This is a close-up image.
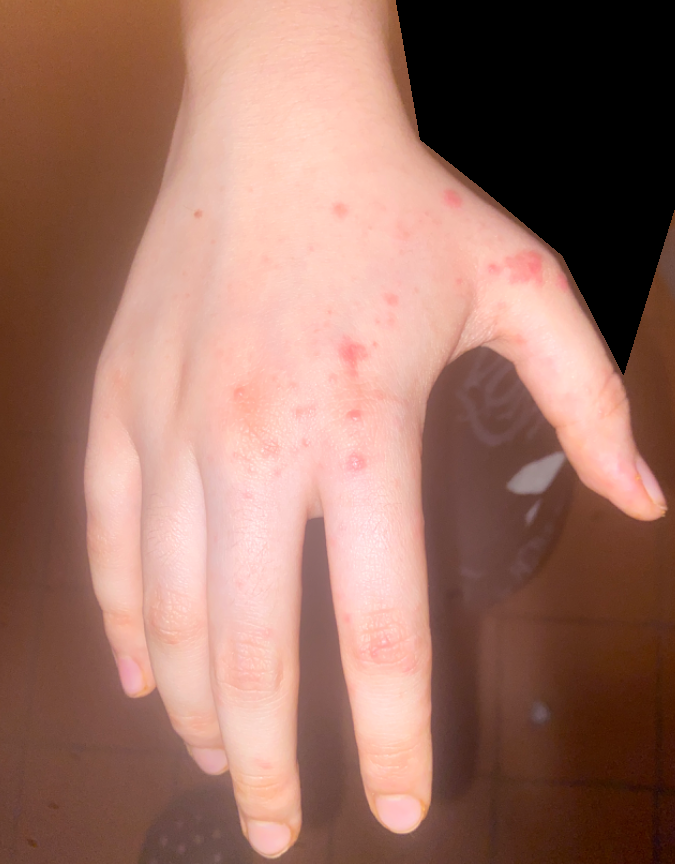Impression:
On remote dermatologist review, Impetigo (weight 0.33); Molluscum Contagiosum (weight 0.33); Allergic Contact Dermatitis (weight 0.33).